The photograph was taken at a distance; symptoms reported: burning, enlargement, bothersome appearance, darkening and itching; the leg and top or side of the foot are involved; skin tone: Fitzpatrick phototype II; no associated systemic symptoms reported; the patient considered this a rash; texture is reported as flat:
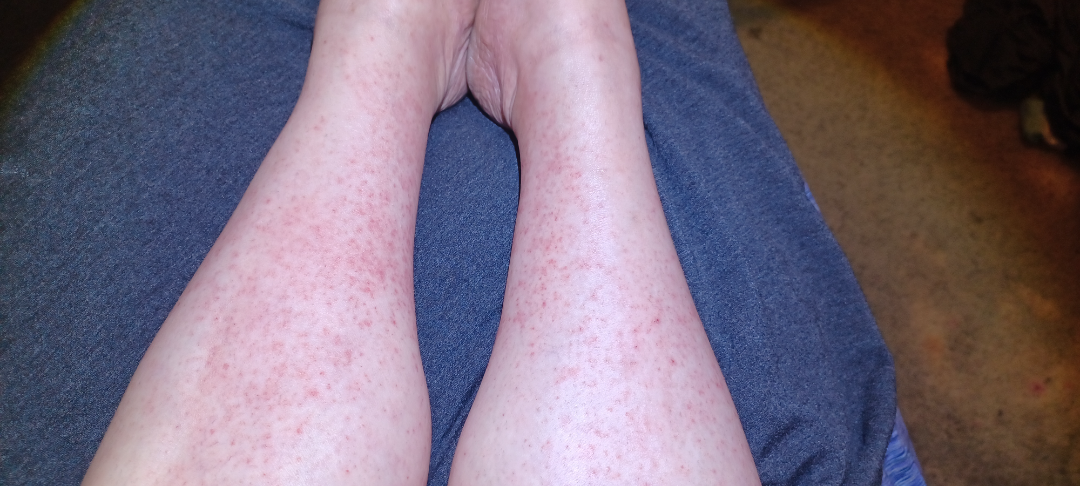<summary>
  <differential>
    <tied_lead>Pigmented purpuric eruption, Leukocytoclastic Vasculitis</tied_lead>
  </differential>
</summary>